Dermoscopy of a skin lesion:
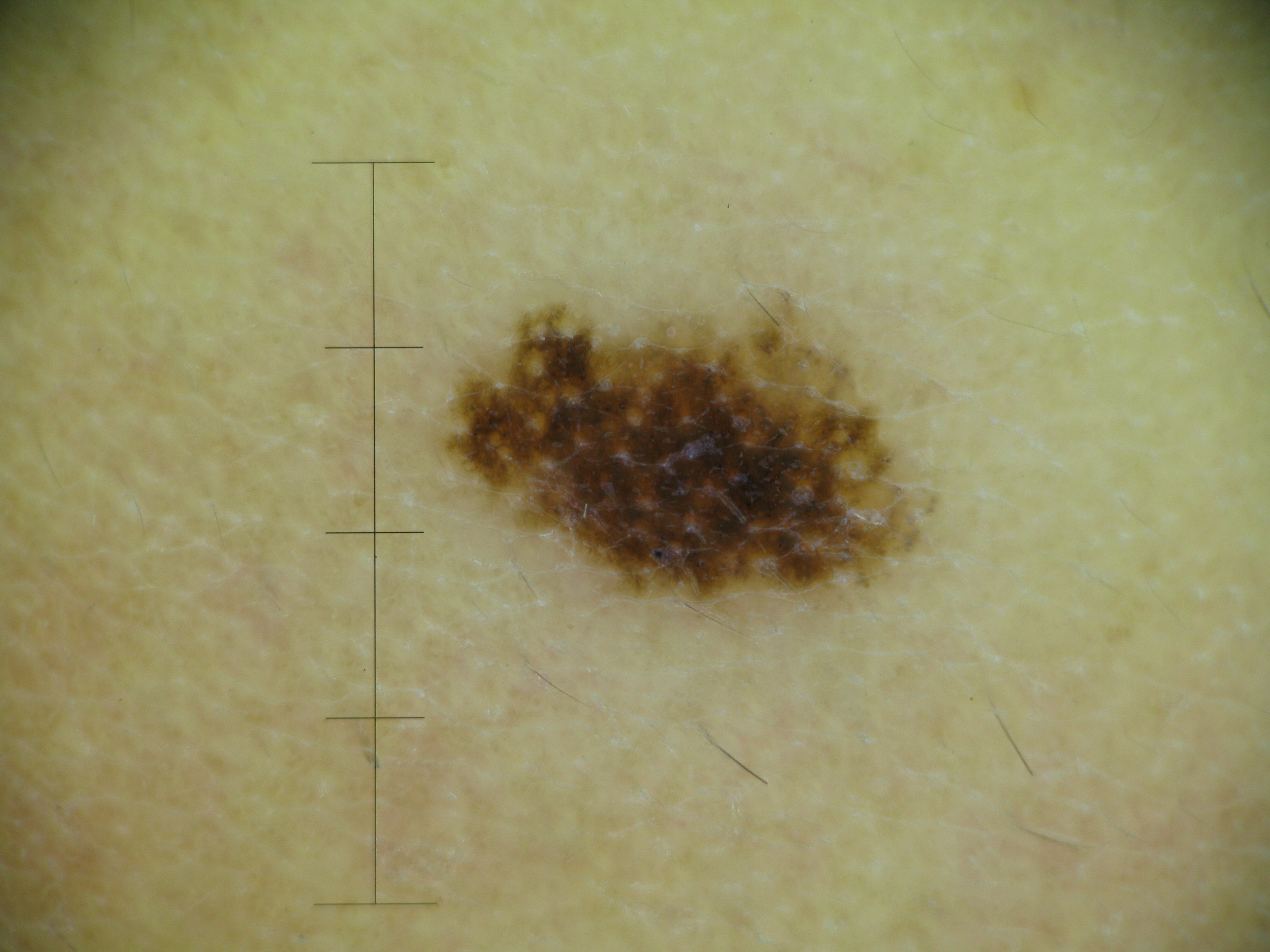Impression:
The diagnosis was a benign lesion — a dysplastic junctional nevus.